A dermoscopic close-up of a skin lesion: 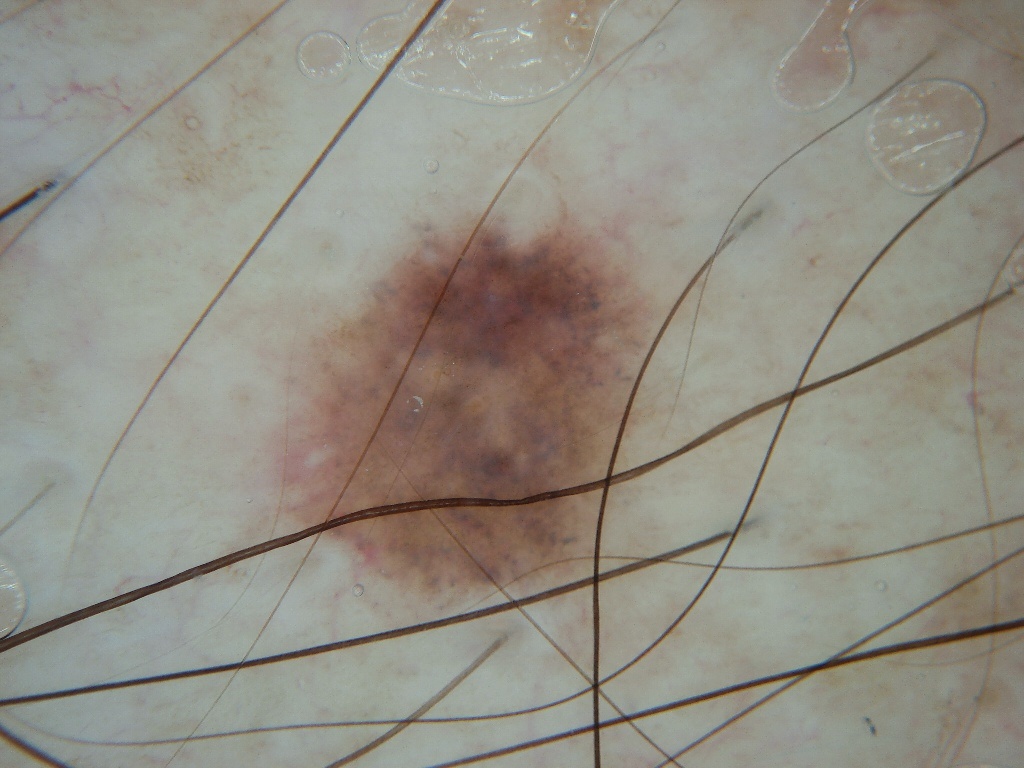lesion location: 246, 180, 679, 638
lesion extent: ~20% of the field
assessment: a benign skin lesion